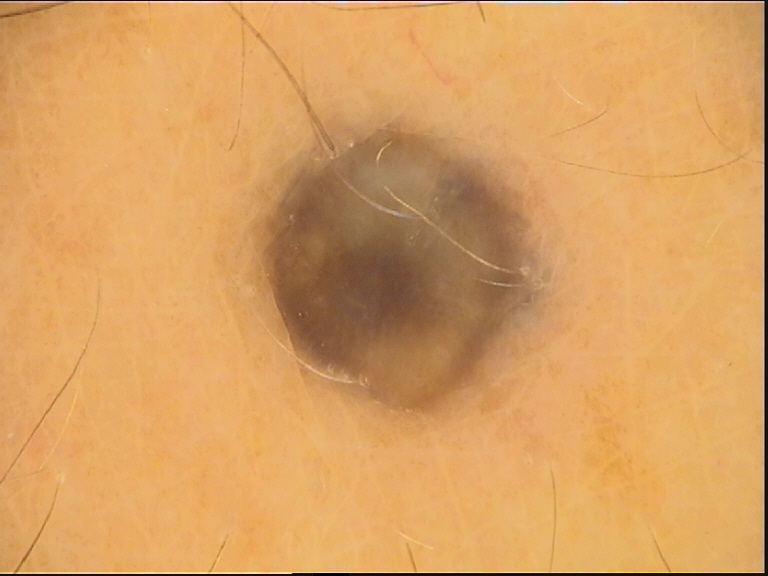Classified as a blue nevus.